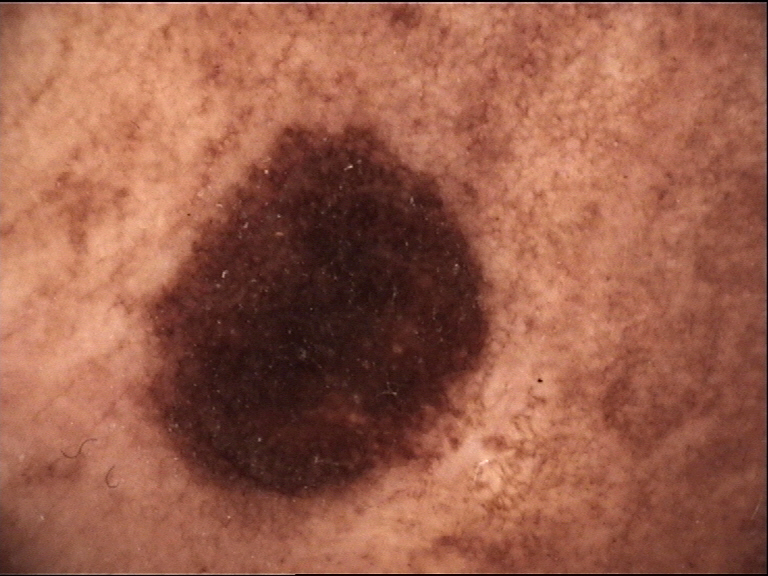Q: What is the imaging modality?
A: dermoscopy
Q: What is this lesion?
A: congenital compound nevus (expert consensus)